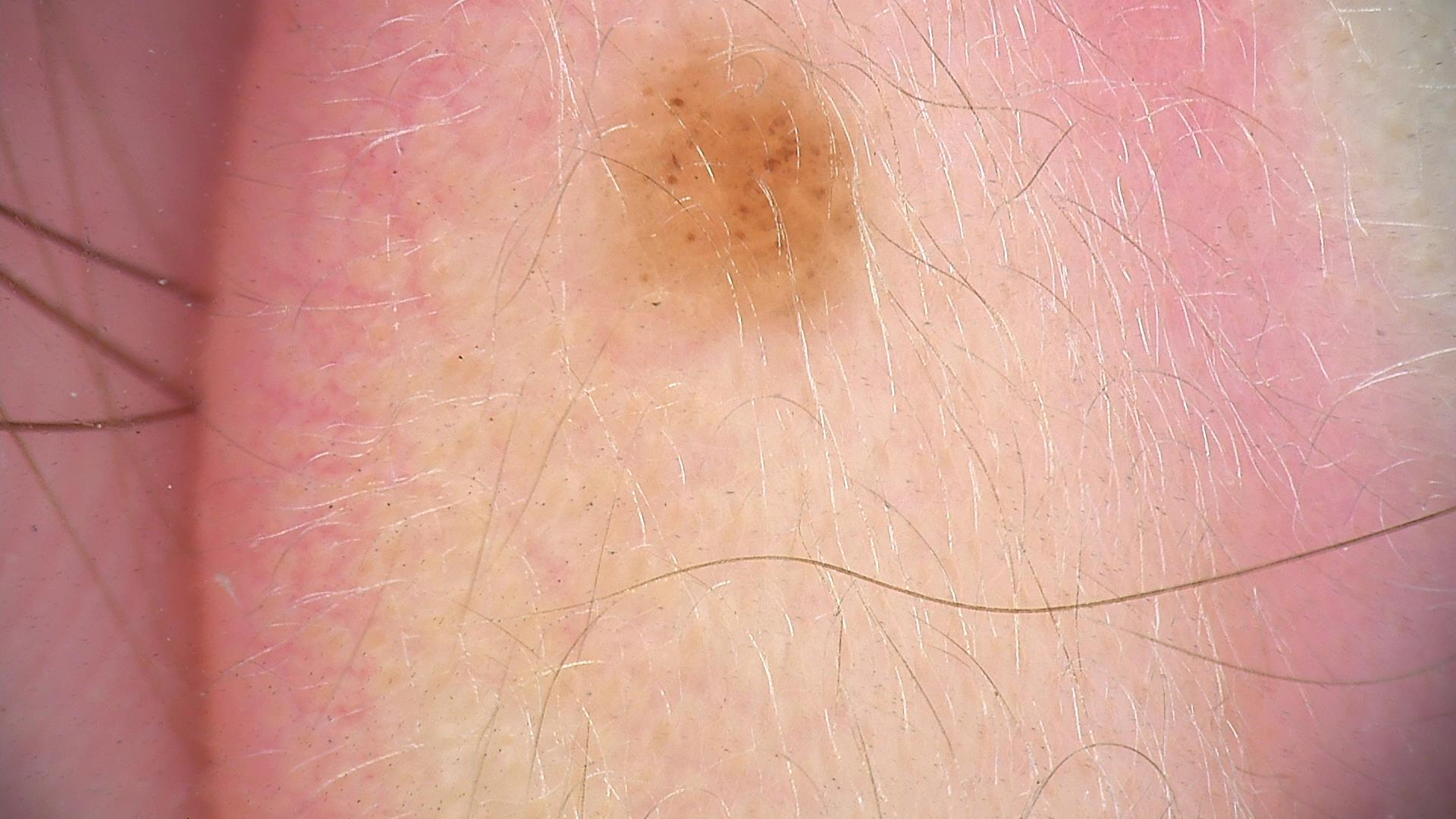A dermoscopic close-up of a skin lesion. Classified as a compound lesion — a Miescher nevus.